A dermatoscopic image of a skin lesion.
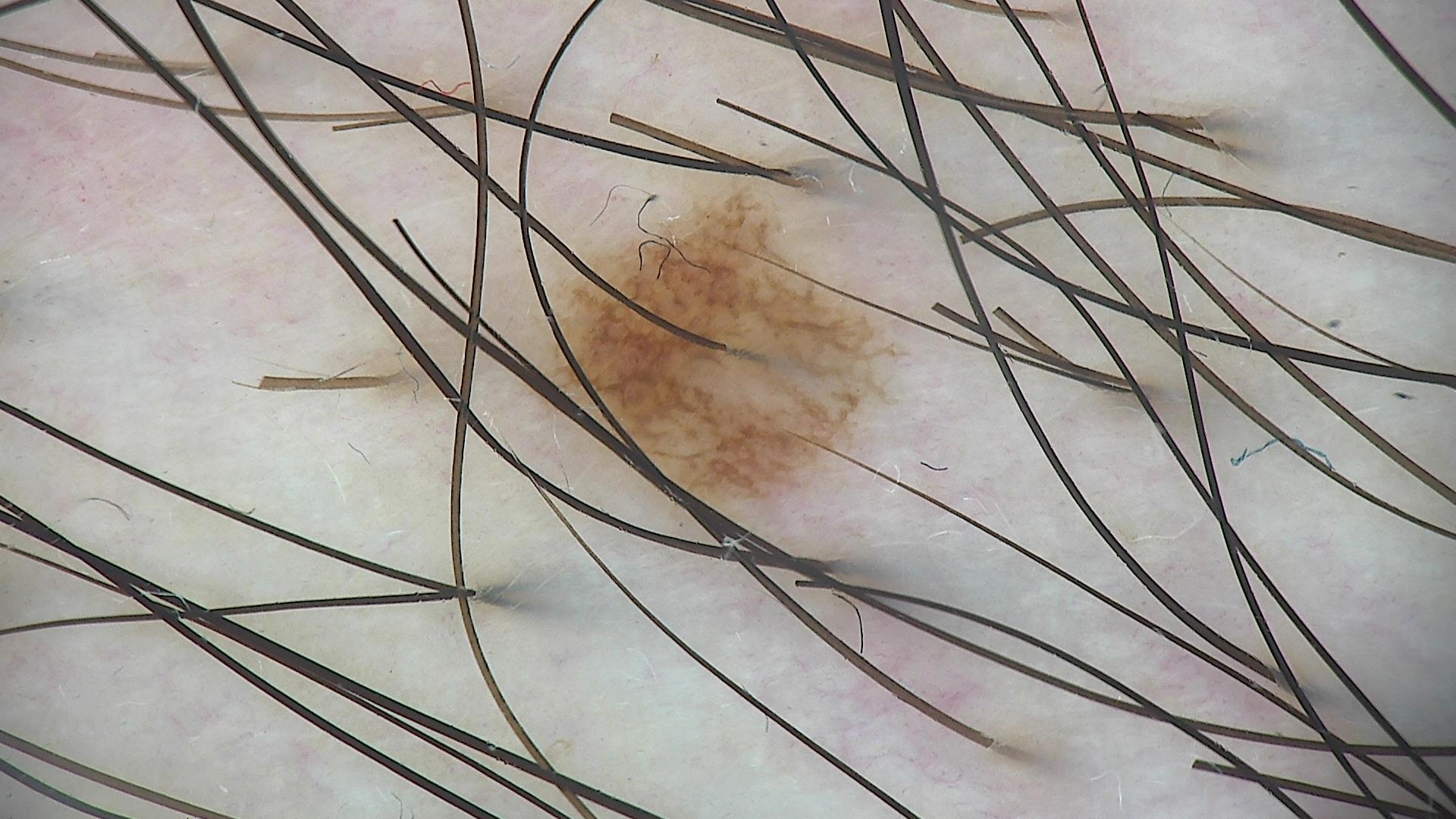label=dysplastic junctional nevus (expert consensus).